A dermoscopic close-up of a skin lesion.
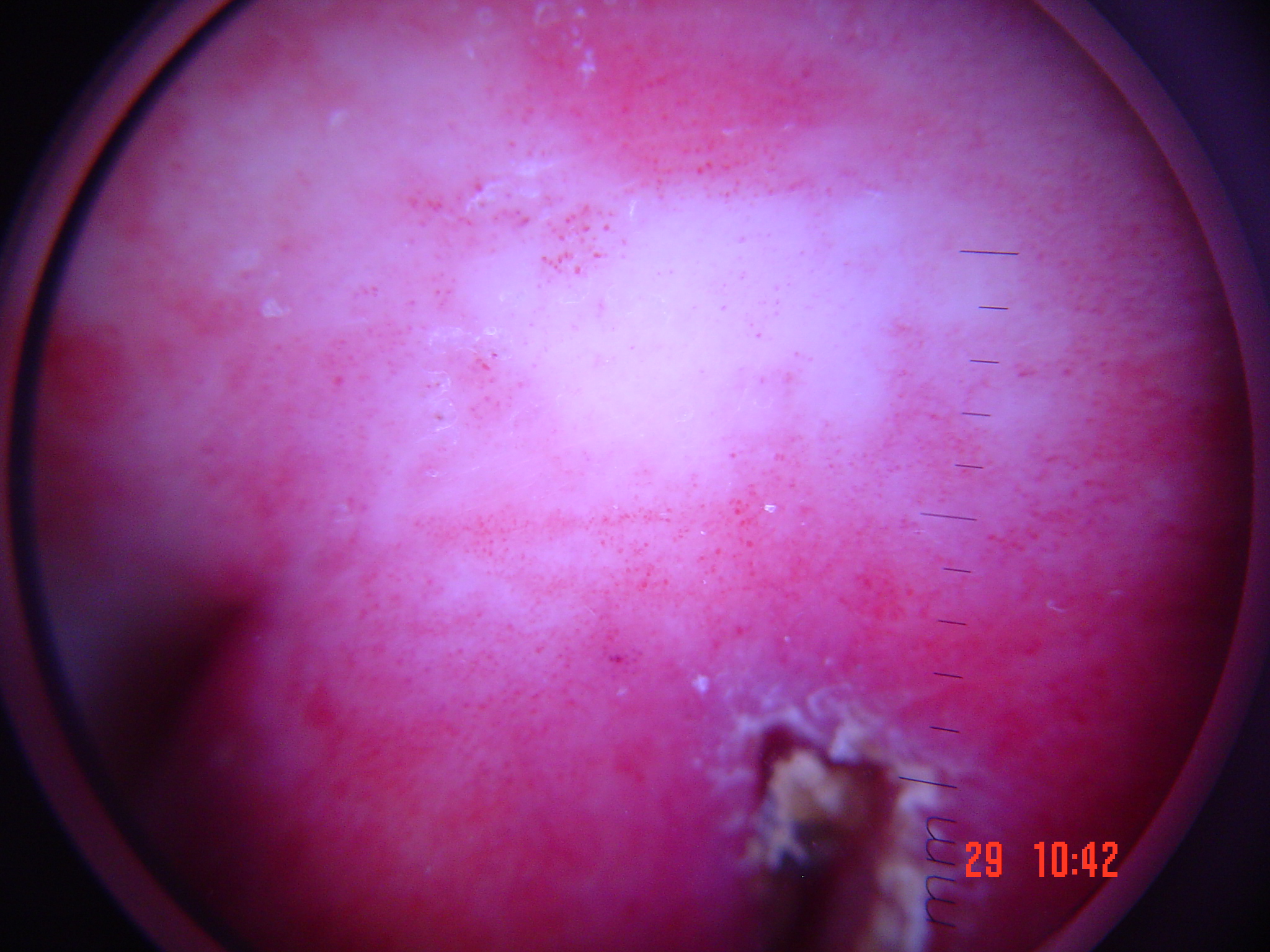Case: The architecture is that of a vascular lesion. Impression: The diagnosis was a hemangioma.